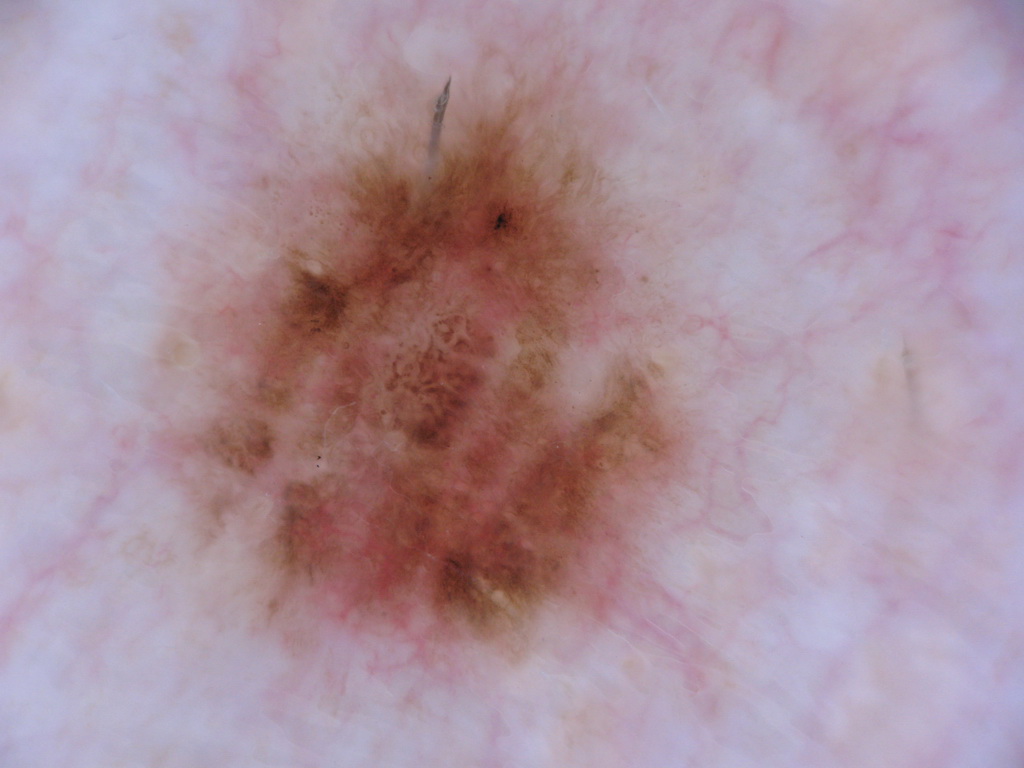subject — male, in their 40s
image type — dermatoscopic image of a skin lesion
dermoscopic findings — pigment network and streaks; absent: negative network, globules, and milia-like cysts
lesion bbox — 160/39/690/663
assessment — a melanocytic nevus